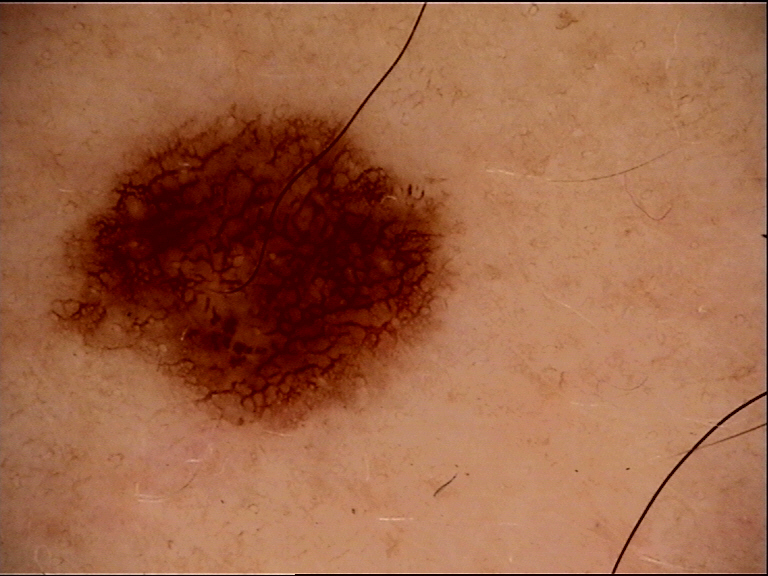Q: What kind of image is this?
A: dermatoscopy
Q: What is the diagnosis?
A: dysplastic junctional nevus (expert consensus)